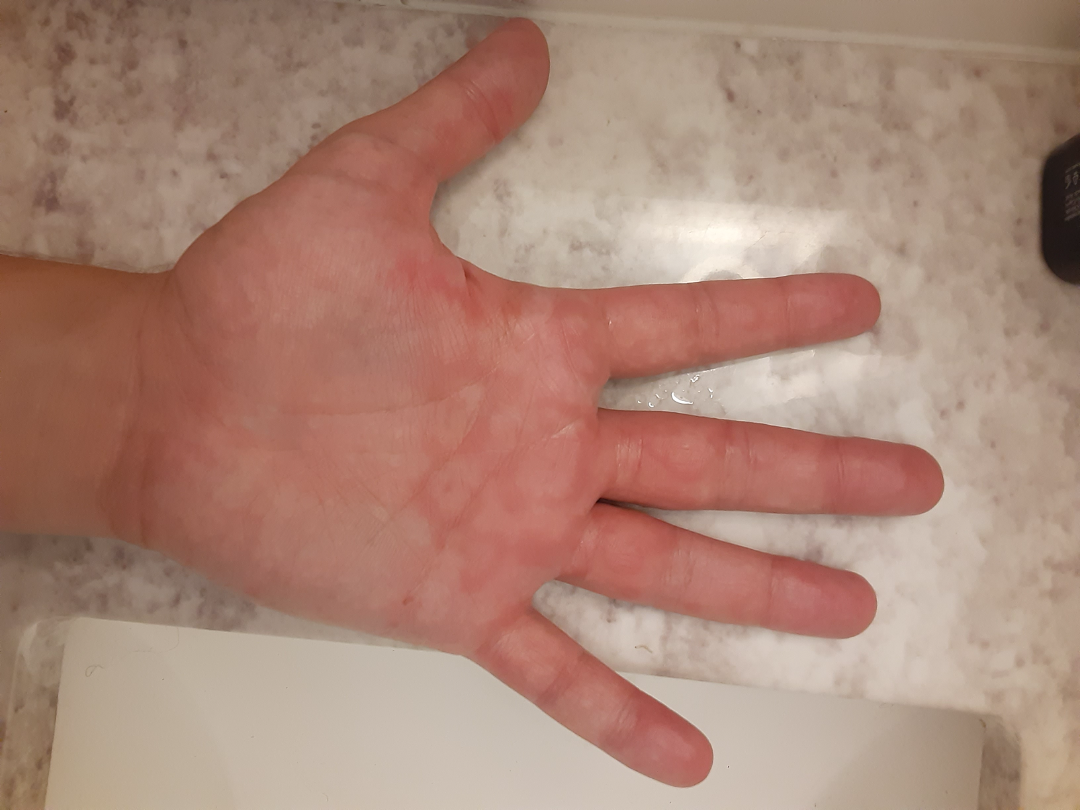Viral Exanthem, Chilblain and Erythema multiforme were considered with similar weight.